Symptoms reported: darkening · the arm and front of the torso are involved · the patient is a female aged 40–49 · no relevant systemic symptoms · a close-up photograph · the contributor notes the lesion is raised or bumpy:
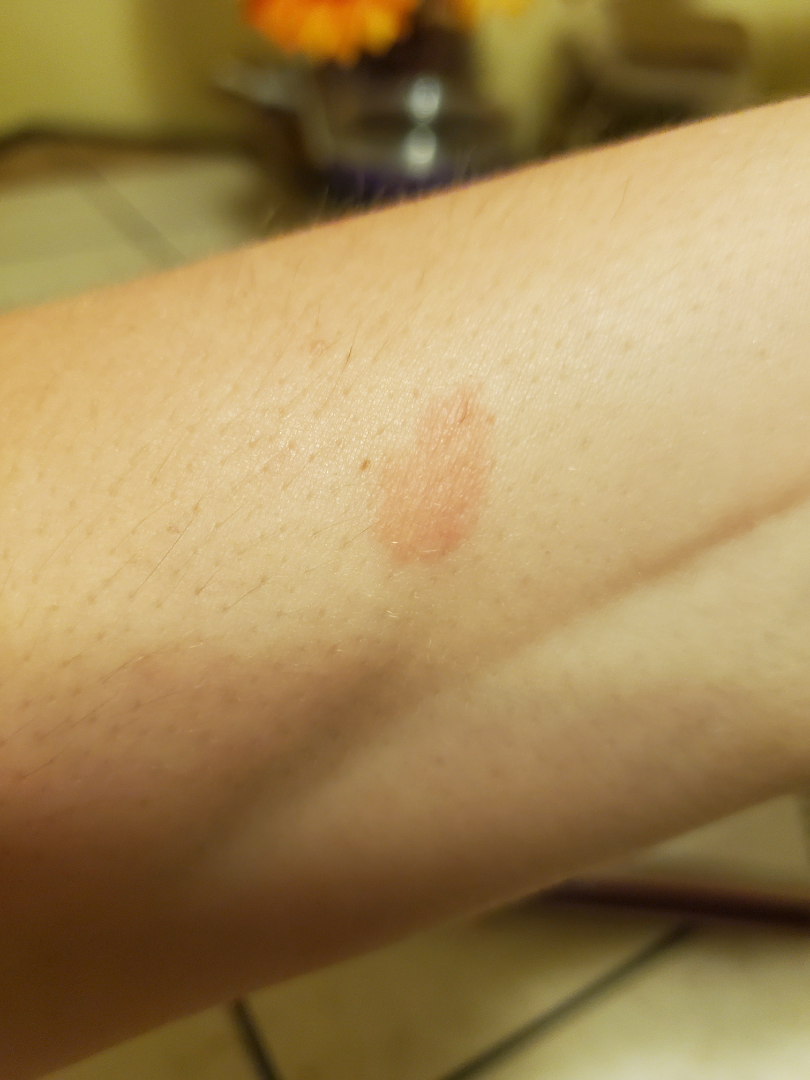{
  "differential": {
    "tied_lead": [
      "SK/ISK",
      "Eczema"
    ],
    "unlikely": [
      "Tinea"
    ]
  }
}